A clinical photograph showing a skin lesion · few moles overall by the patient's own estimate — 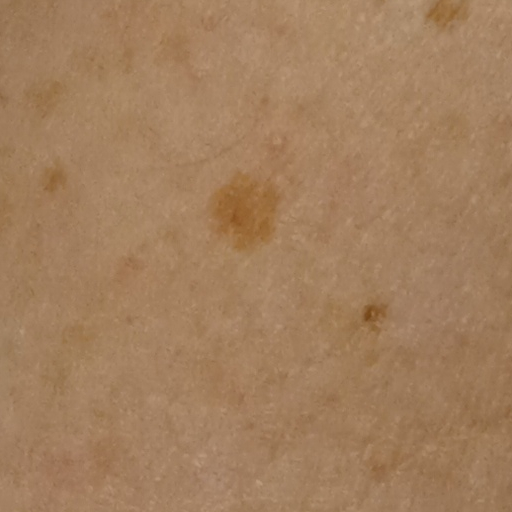Summary:
The lesion involves an arm.
Assessment:
Dermatologist review favored a melanocytic nevus.